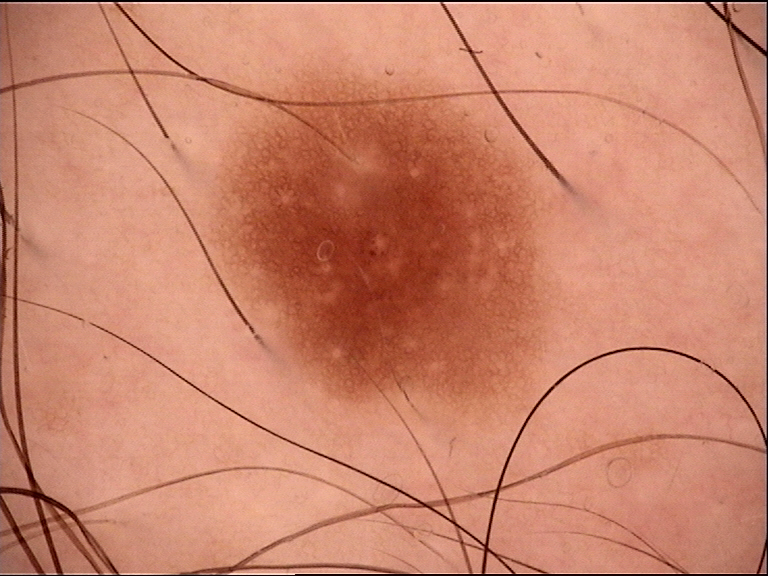{
  "diagnosis": {
    "name": "dysplastic junctional nevus",
    "code": "jd",
    "malignancy": "benign",
    "super_class": "melanocytic",
    "confirmation": "expert consensus"
  }
}